The photograph is a close-up of the affected area, located on the arm, reported duration is less than one week, the patient considered this a rash — 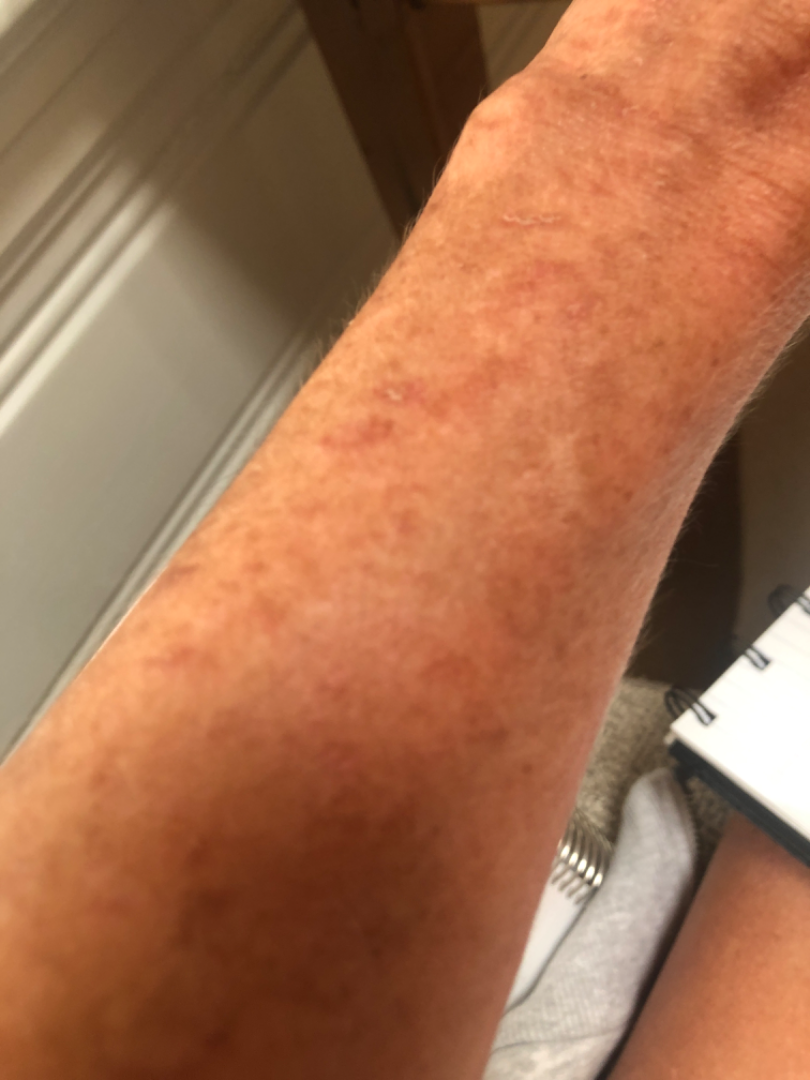The case was indeterminate on photographic review.